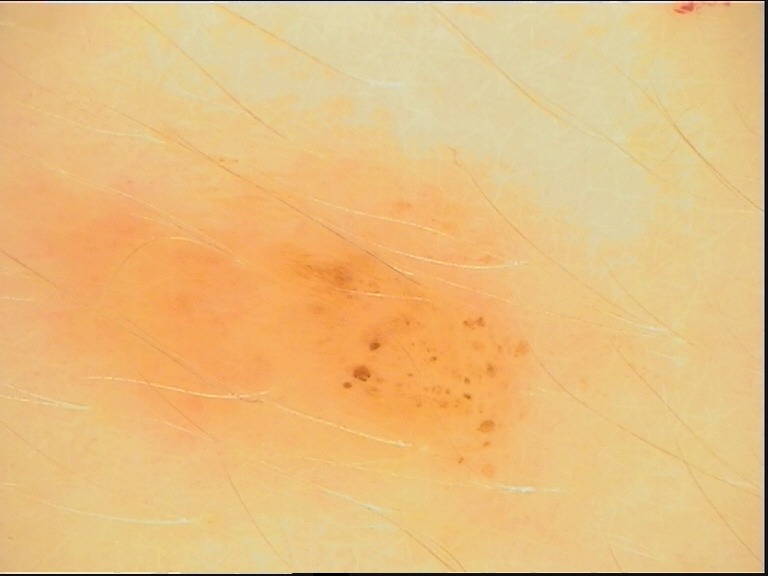The diagnosis was a benign lesion — a dysplastic junctional nevus.